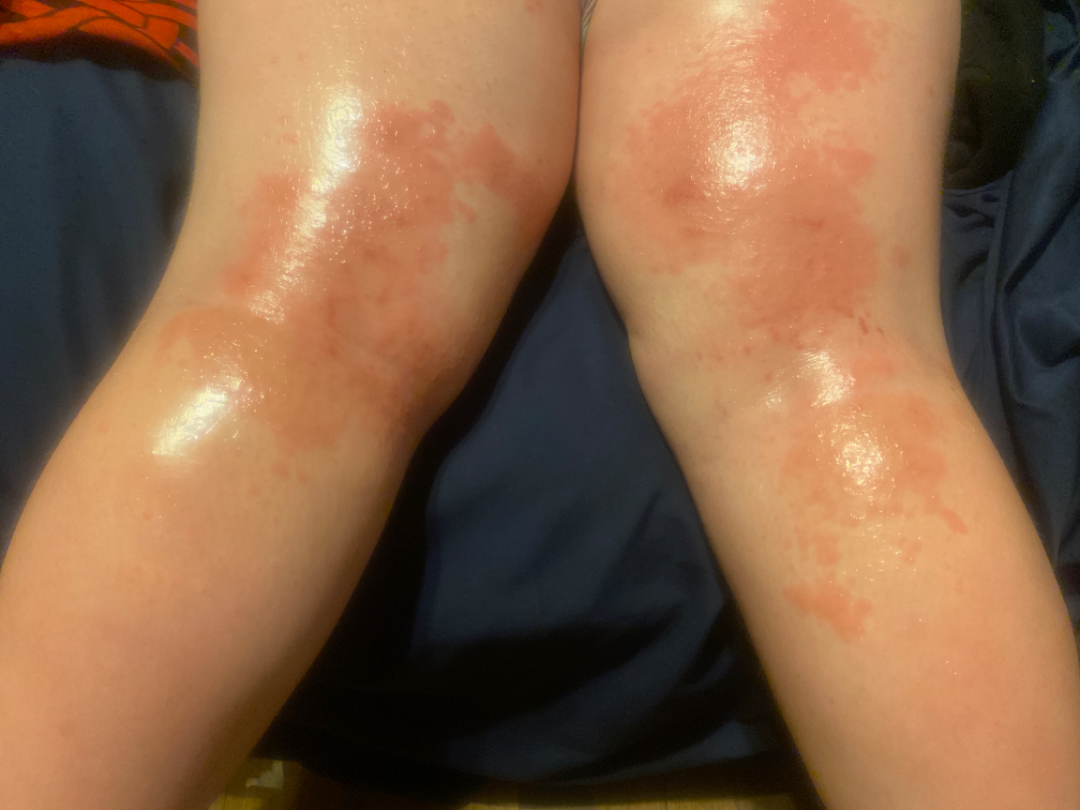differential:
  leading:
    - Allergic Contact Dermatitis
  considered:
    - Eczema
  unlikely:
    - Psoriasis